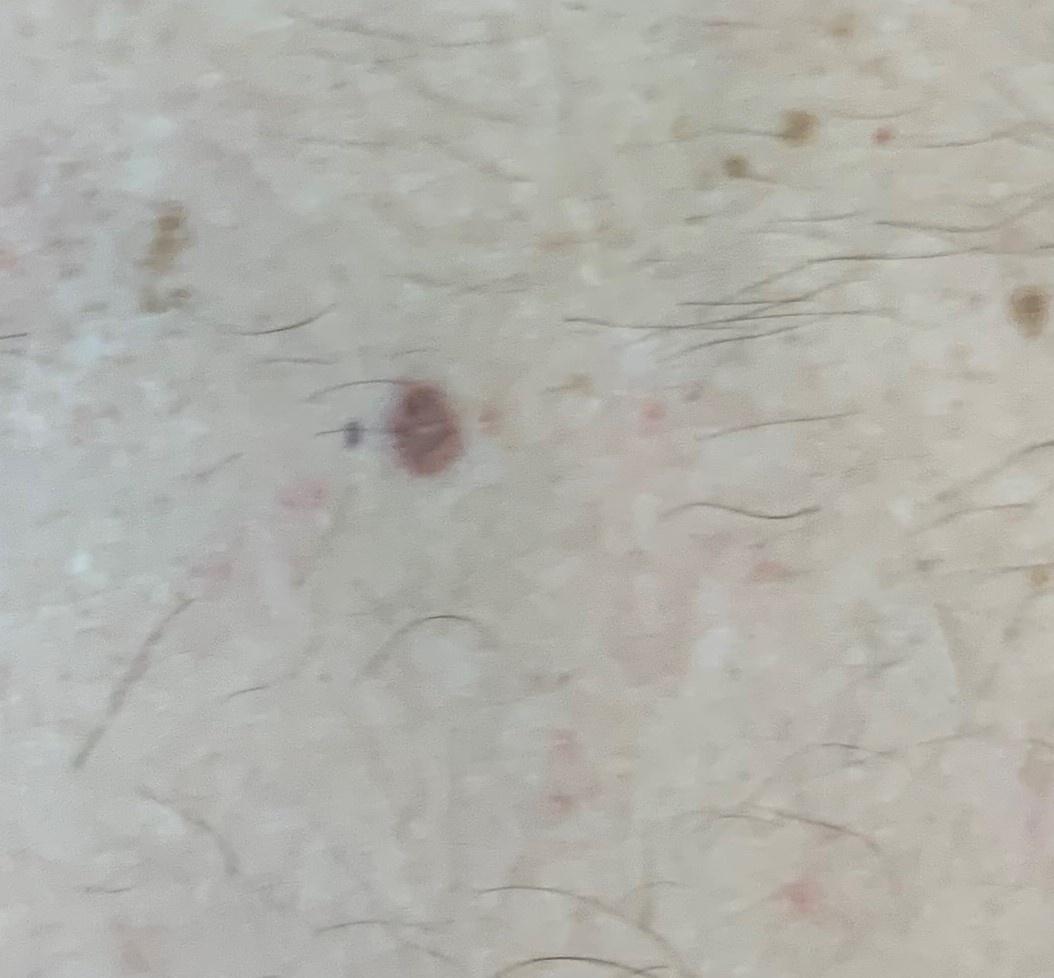{"image": "clinical overview photograph", "patient": {"age_approx": 70, "sex": "male"}, "diagnosis": {"name": "Basal cell carcinoma", "malignancy": "malignant", "confirmation": "histopathology", "lineage": "adnexal"}}